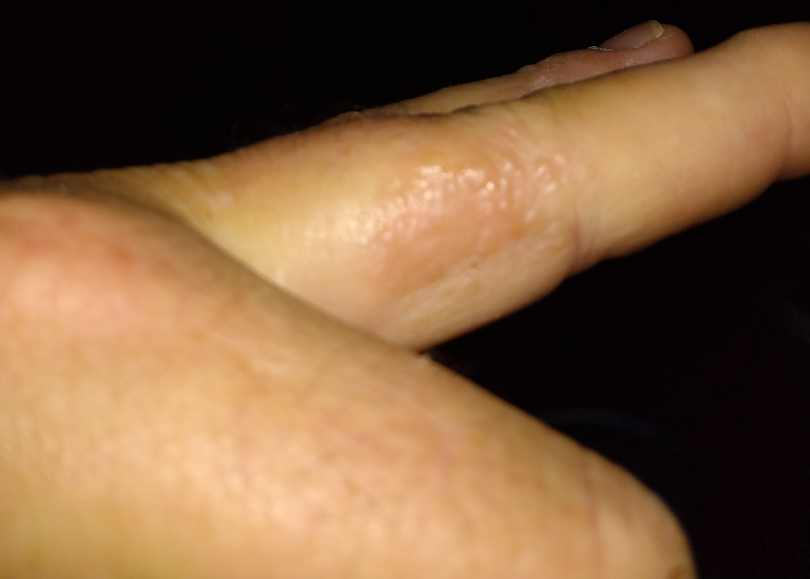<dermatology_case>
  <differential>
    <leading>Eczema</leading>
    <considered>Allergic Contact Dermatitis</considered>
  </differential>
</dermatology_case>